The patient considered this a rash · this image was taken at an angle · the head or neck, arm, leg and palm are involved · the subject is a female aged 18–29 · the condition has been present for more than one year · associated systemic symptoms include joint pain and shortness of breath · symptoms reported: bothersome appearance: 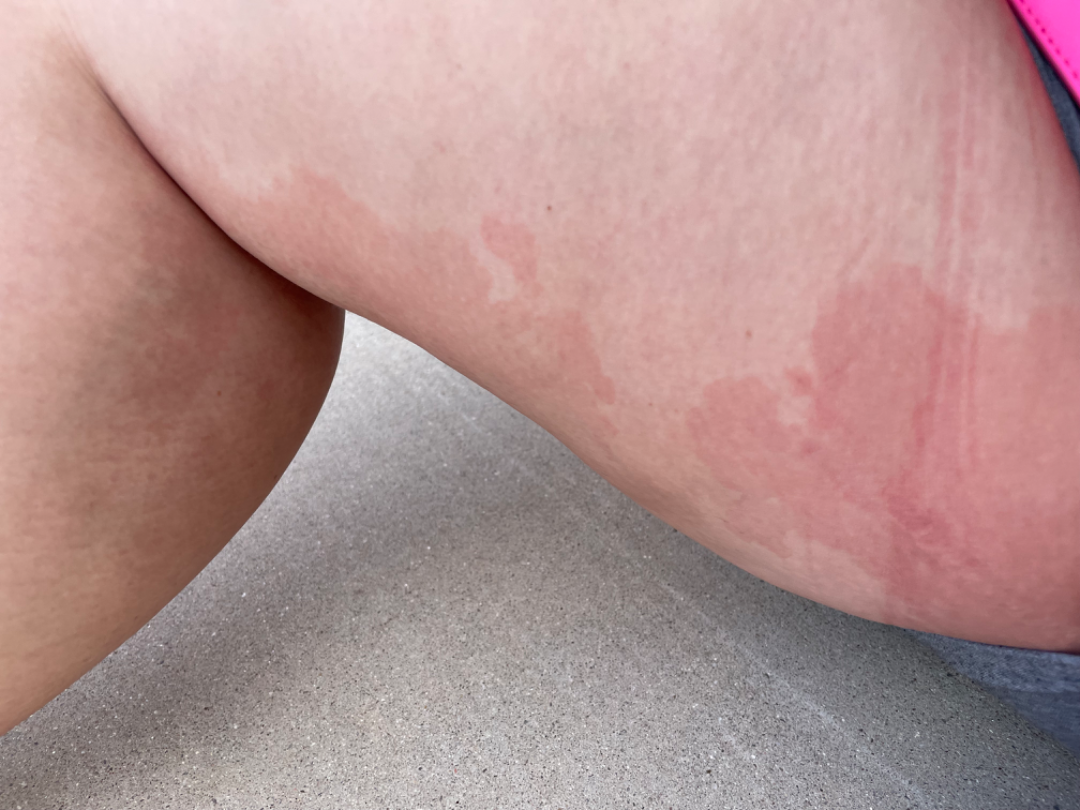Findings:
• clinical impression: most consistent with Eczema; also consider Viral Exanthem; with consideration of Urticaria